By self-report, a personal history of cancer, a personal history of skin cancer, no immunosuppression, and no family history of skin cancer; the patient says their skin tans without first burning; the patient describes having few moles overall; the referring clinician suspected basal cell carcinoma.
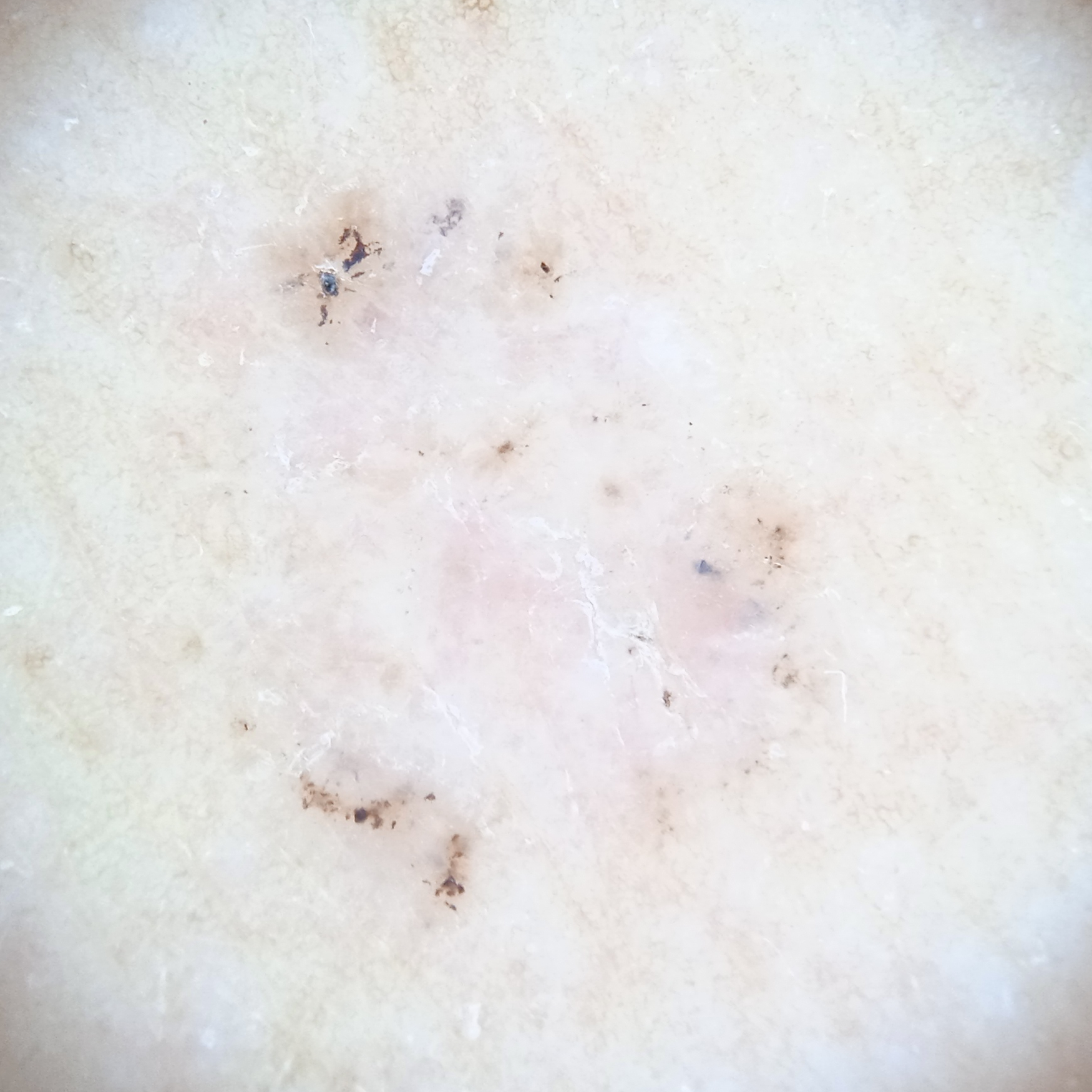Summary: The lesion involves the back. The lesion measures approximately 7.8 mm. Impression: The dermatologists' assessment was a basal cell carcinoma.